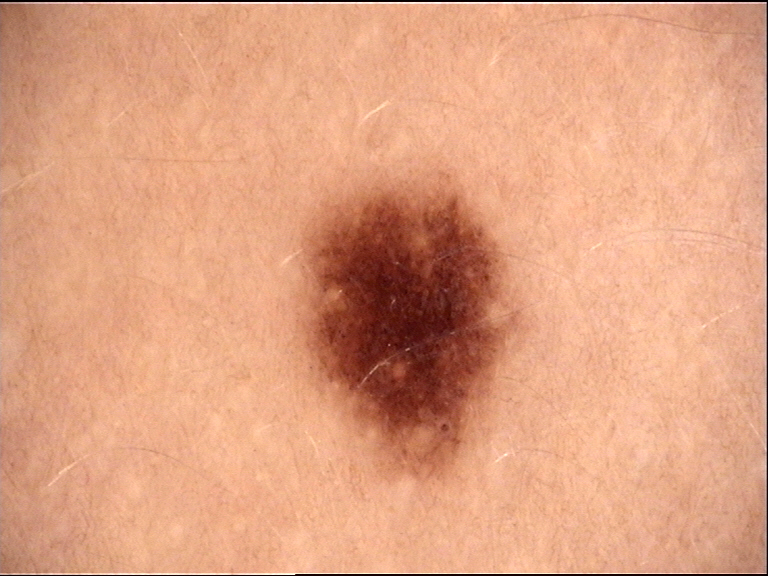class = dysplastic junctional nevus (expert consensus)